Dermoscopy of a skin lesion:
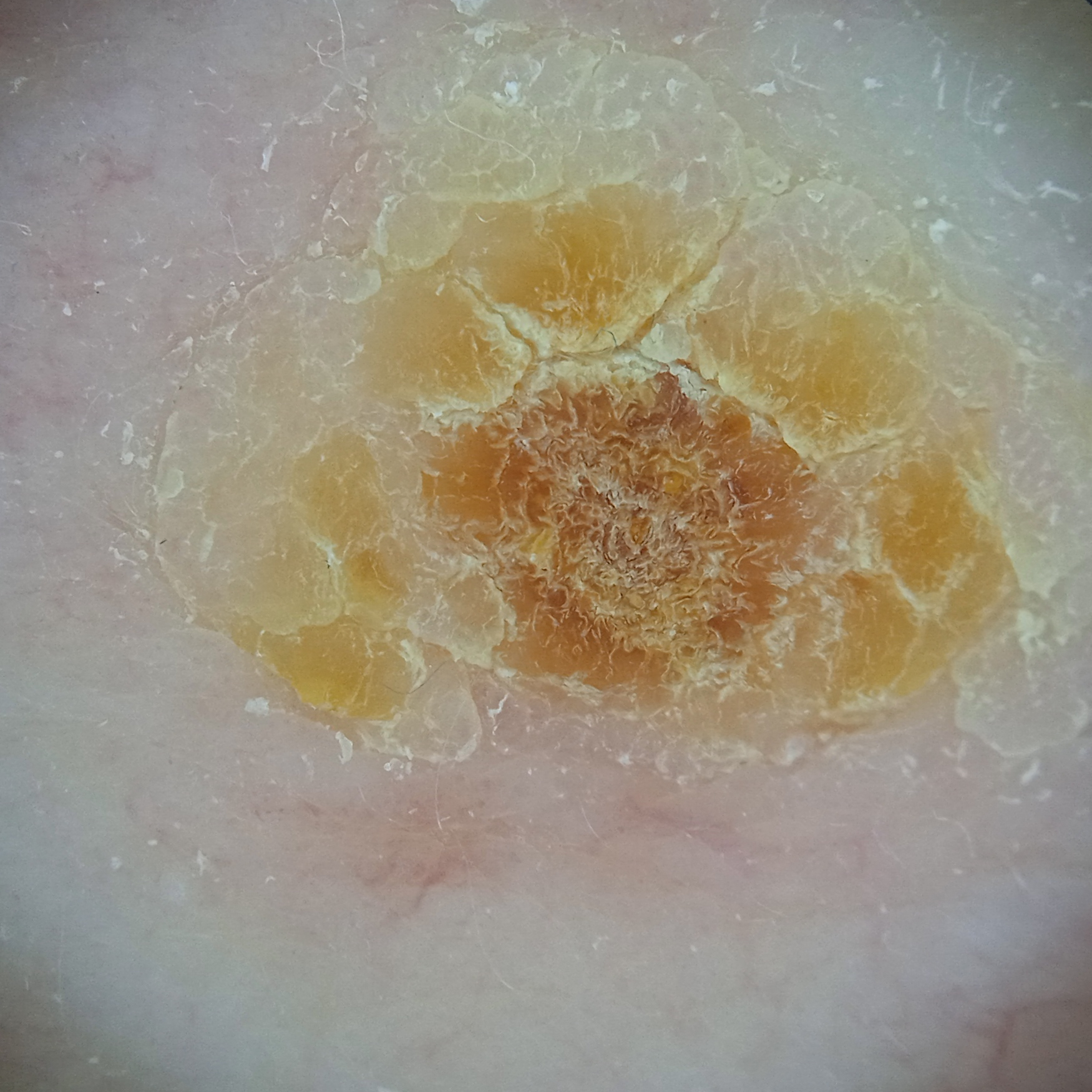– size · 11.1 mm
– assessment · actinic keratosis (dermatologist consensus)